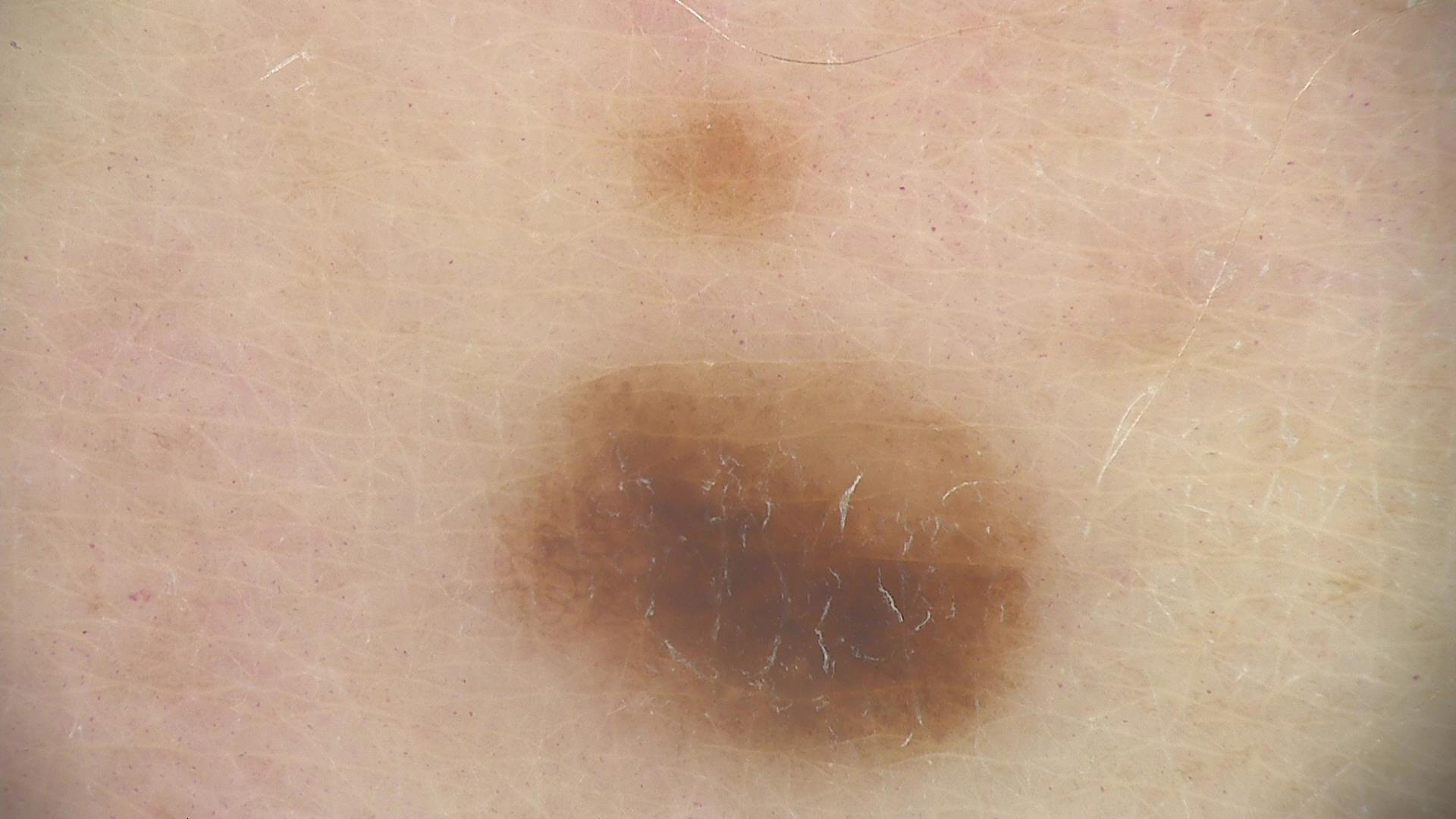Case:
* imaging · dermatoscopy
* diagnostic label · dysplastic junctional nevus (expert consensus)